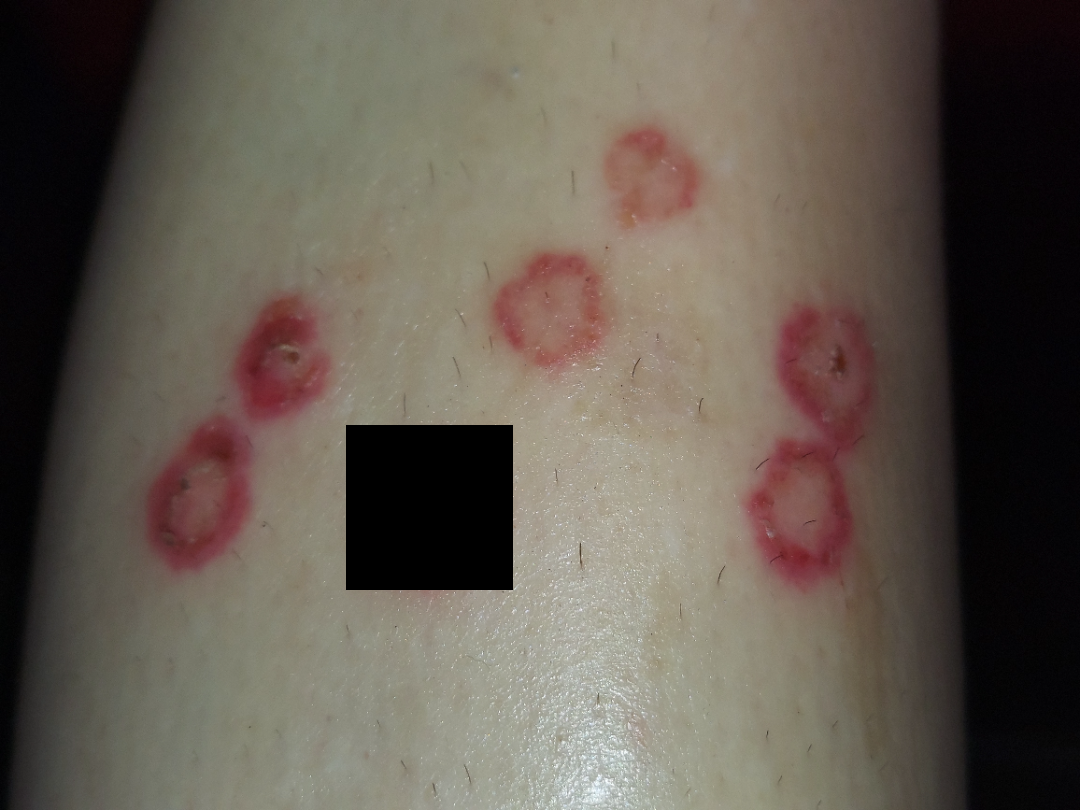The condition could not be reliably identified from the image.